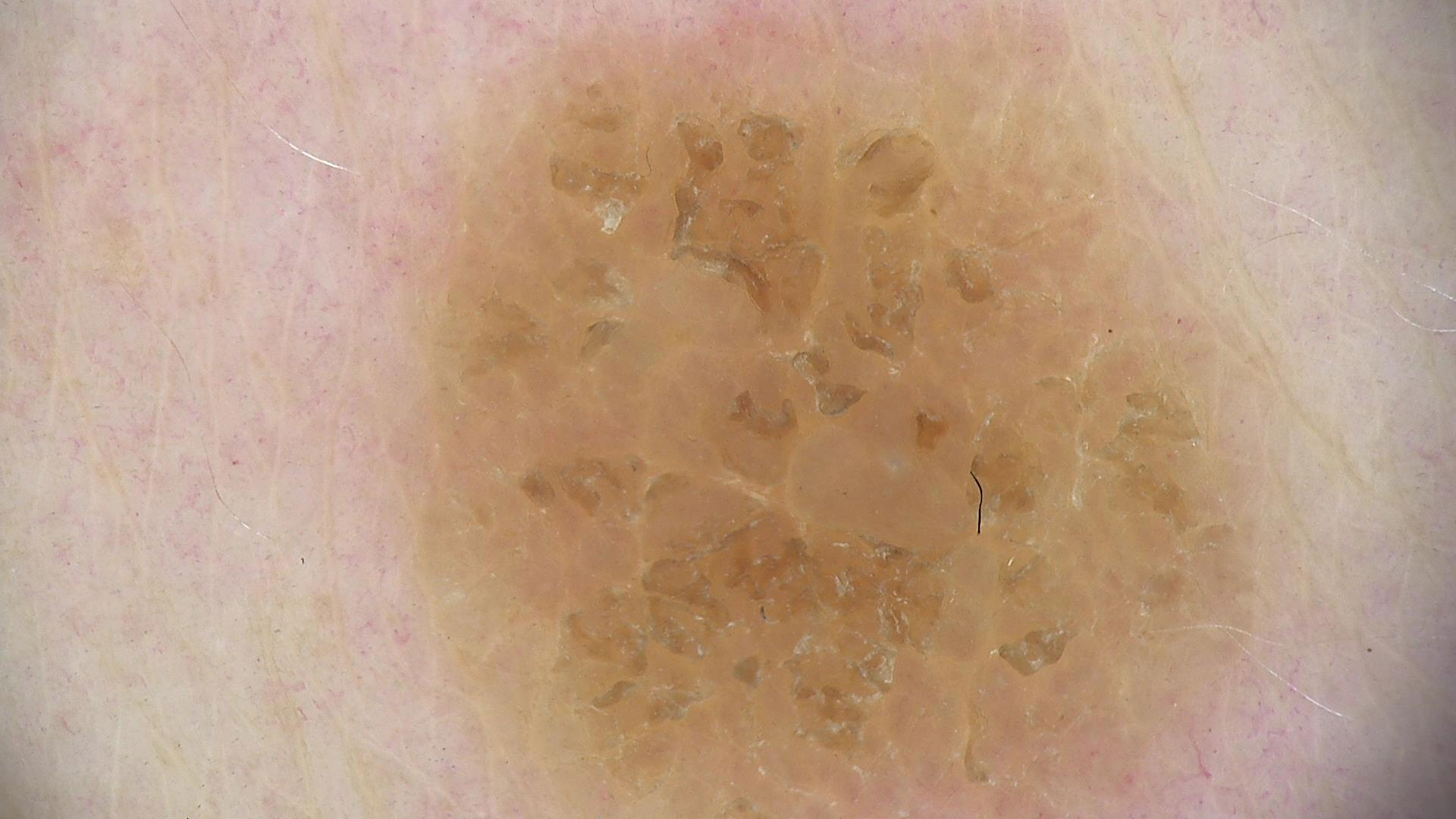A dermoscopic close-up of a skin lesion.
The architecture is that of a keratinocytic lesion.
Consistent with a seborrheic keratosis.